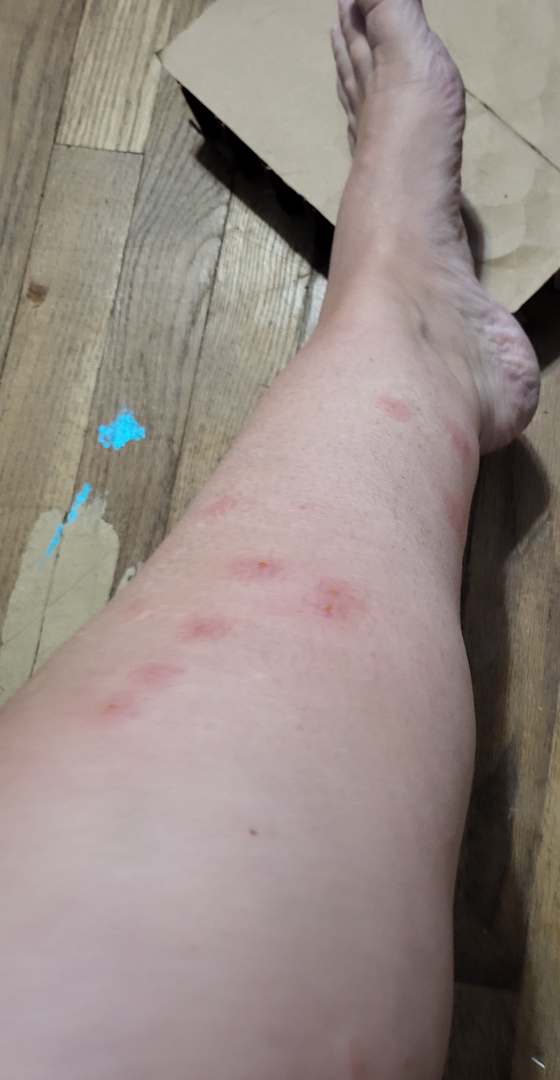| feature | finding |
|---|---|
| assessment | most consistent with Insect Bite; the differential also includes Localized skin infection; possibly Allergic Contact Dermatitis |